The patient considered this a rash, the condition has been present for about one day, the patient is male, the lesion involves the arm, symptoms reported: itching, the patient reported no systemic symptoms, the photograph was taken at a distance.
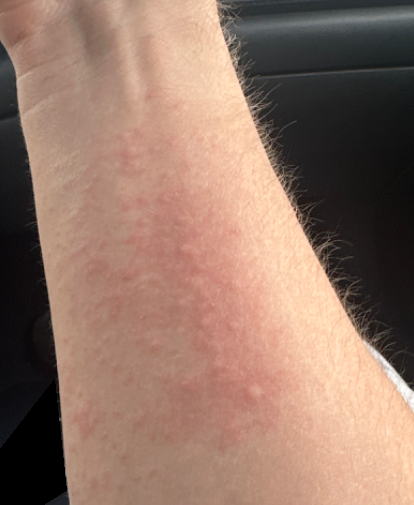Impression: The reviewing panel's impression was: Urticaria (most likely); Allergic Contact Dermatitis (considered); Eczema (less likely).